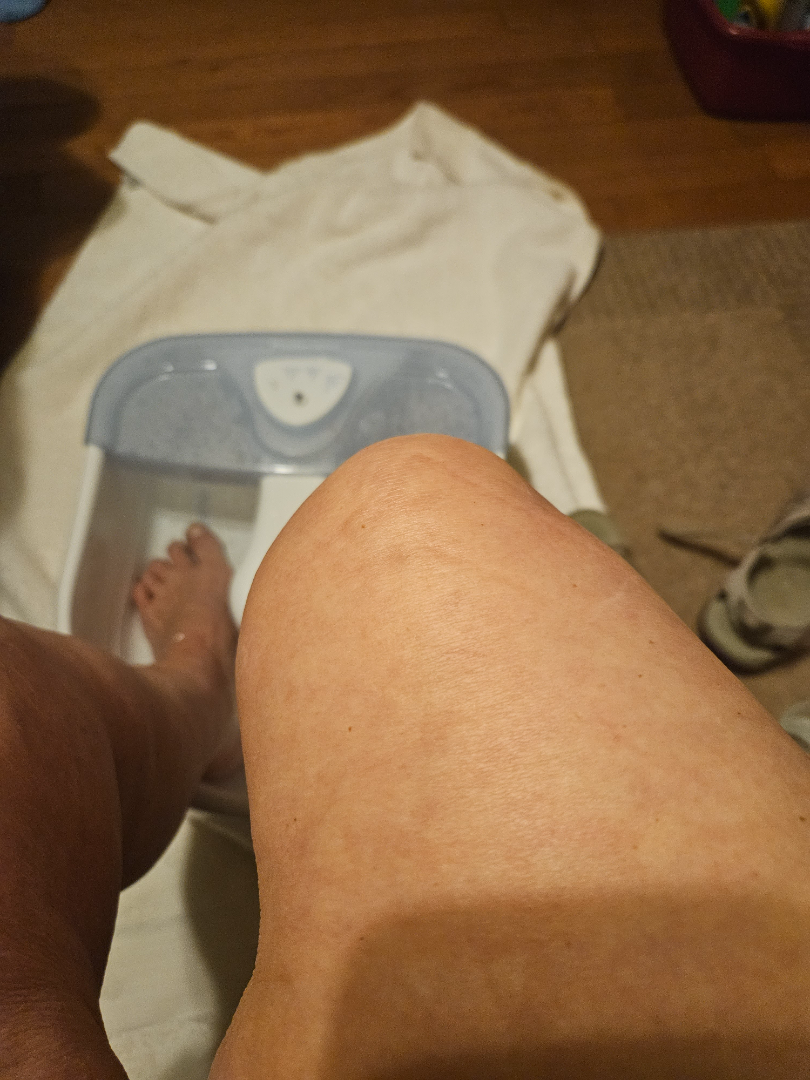assessment = indeterminate | framing = close-up.